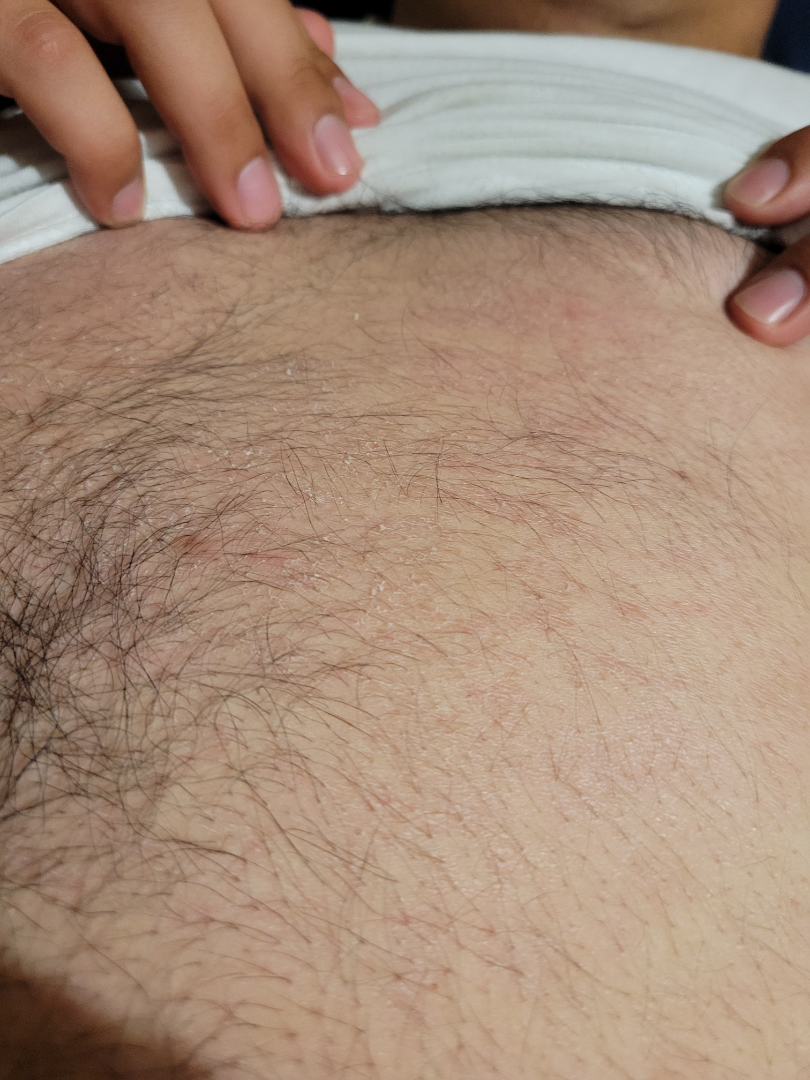impression: favoring Eczema; also raised was Pityriasis lichenoides; the differential also includes Tinea